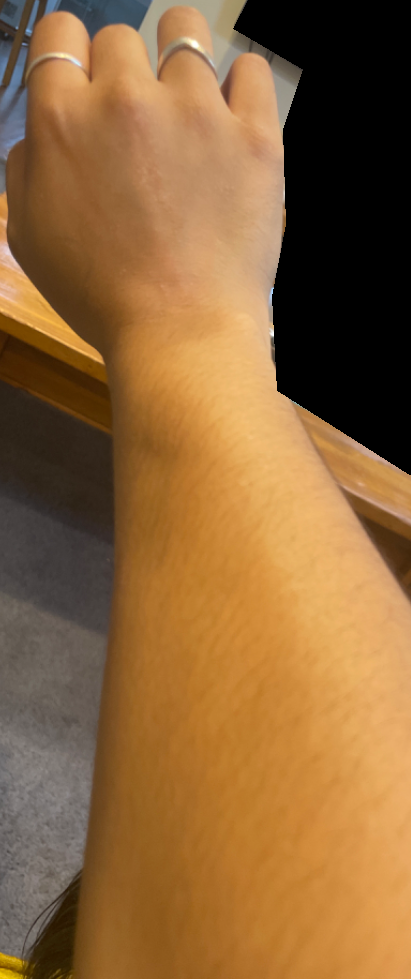Case summary:
- patient · female, age 18–29
- location · arm
- view · at a distance
- clinical impression · Verruca vulgaris and Lichen planus/lichenoid eruption were each considered, in no particular order; lower on the differential is Lichen nitidus; less probable is Skin hypopigmented; less likely is Chronic dermatitis, NOS; a remote consideration is Eczema